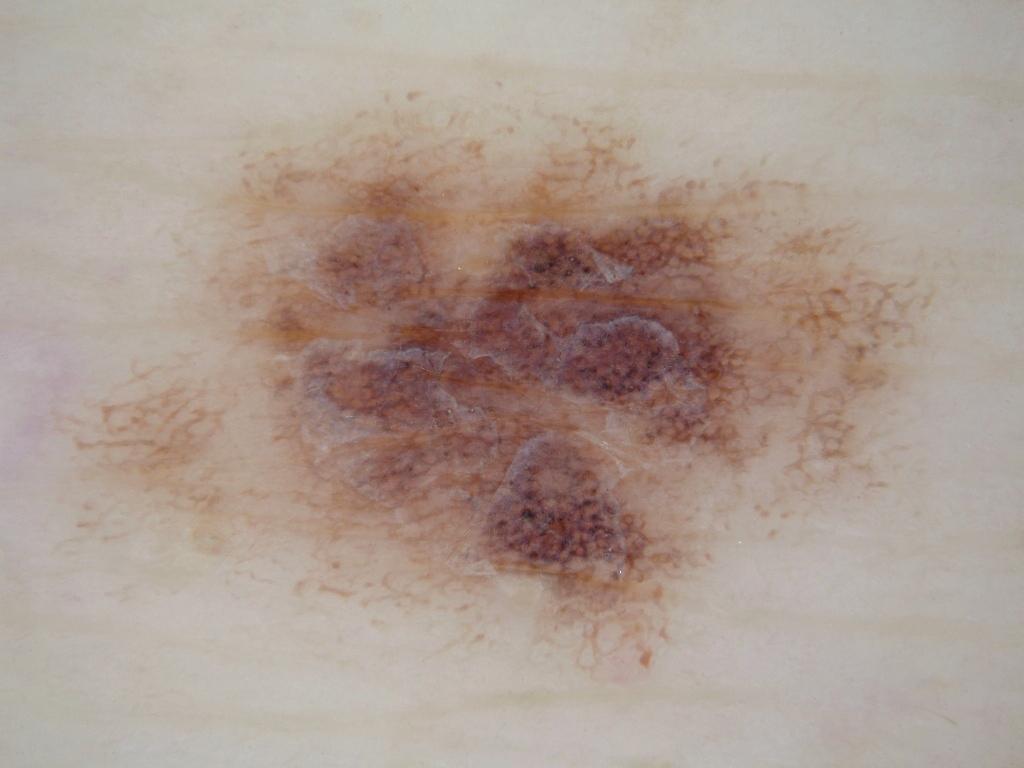A dermoscopic close-up of a skin lesion. With coordinates (x1, y1, x2, y2), the lesion spans 40 76 986 691. Dermoscopic examination shows pigment network and globules. The diagnostic assessment was a melanocytic nevus.